A dermoscopy image of a single skin lesion: 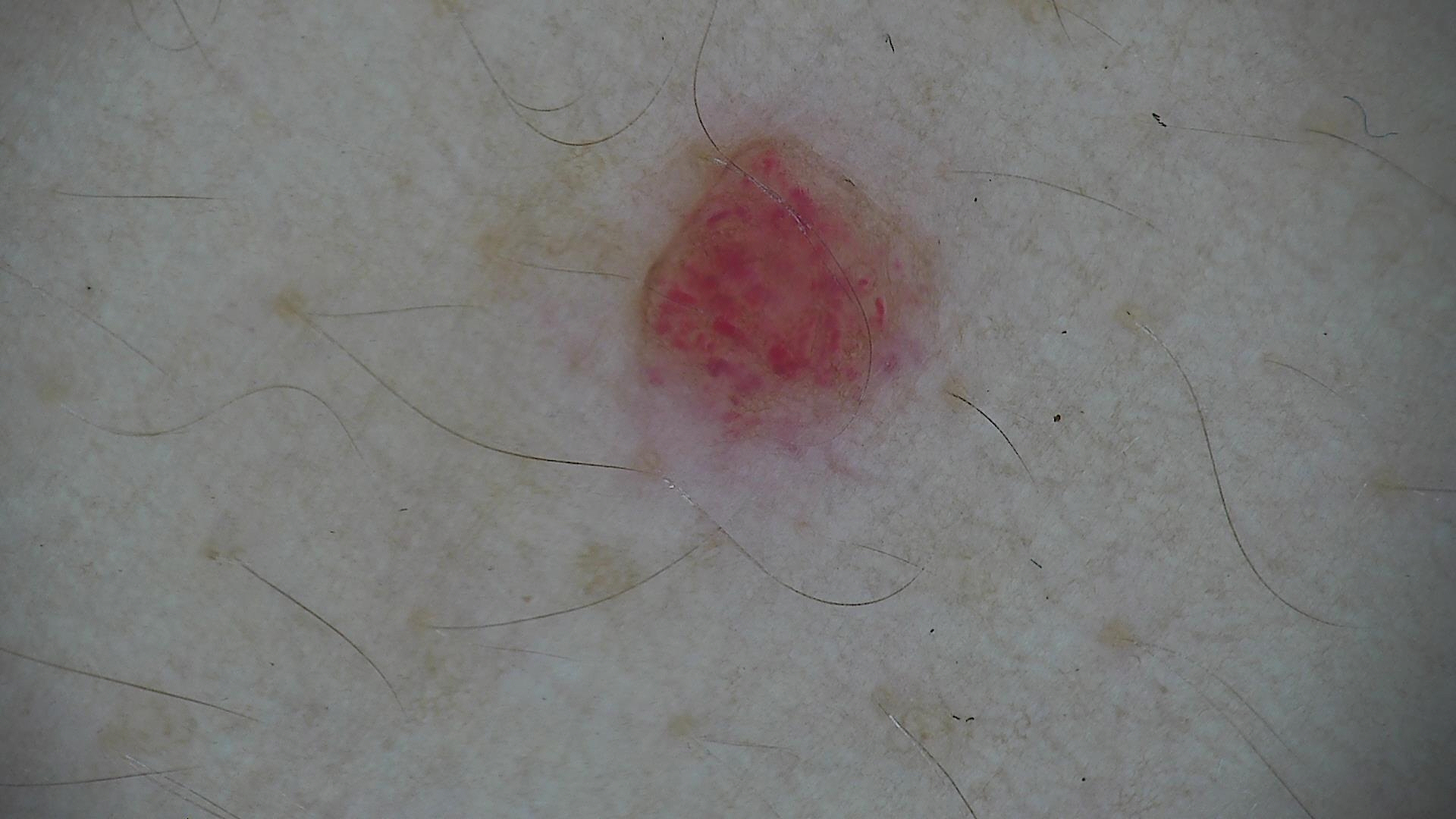| feature | finding |
|---|---|
| lesion type | vascular |
| label | hemangioma (expert consensus) |